The contributor notes the condition has been present for one to four weeks · the patient considered this a rash · no constitutional symptoms were reported · texture is reported as fluid-filled · this is a close-up image · the contributor notes itching · the contributor is a female aged 18–29 · the lesion involves the arm: 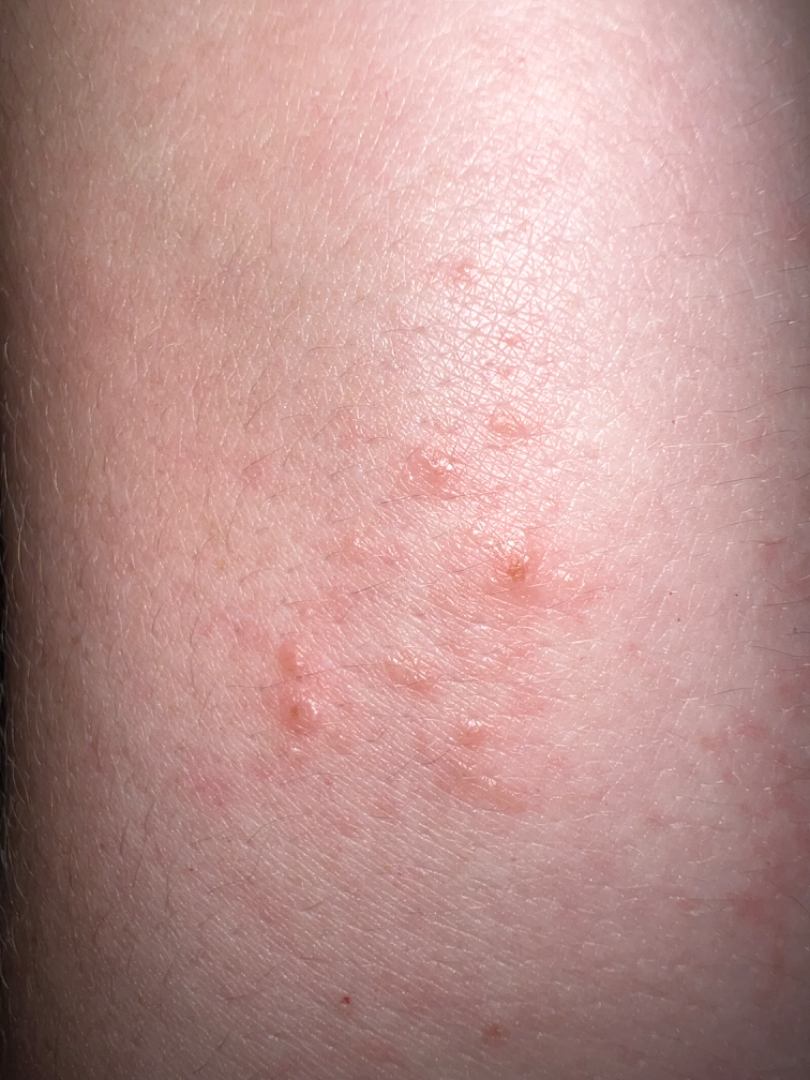<report>
<differential>Allergic Contact Dermatitis</differential>
</report>